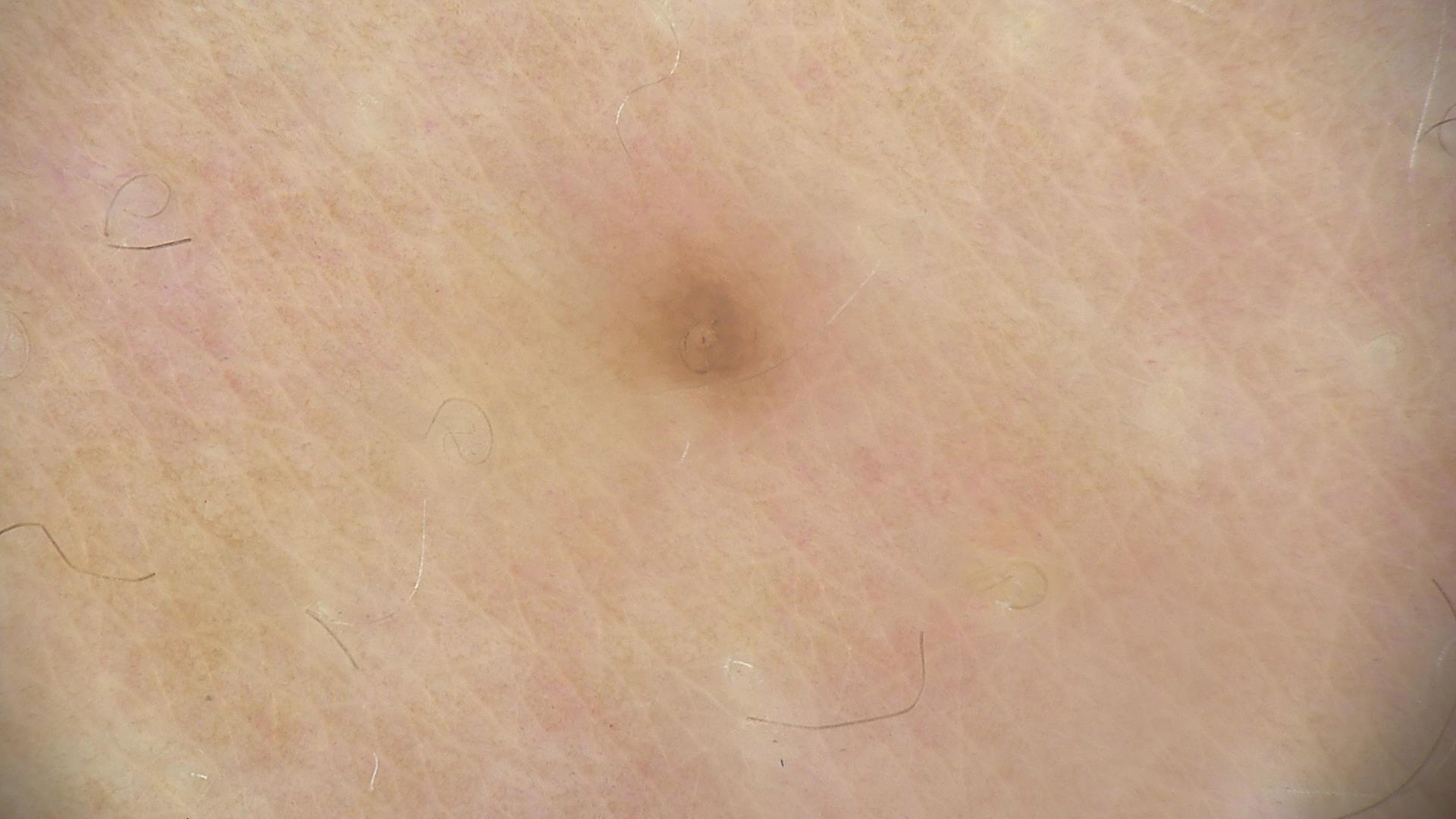Summary: A dermoscopic image of a skin lesion. Conclusion: The diagnosis was a junctional nevus.